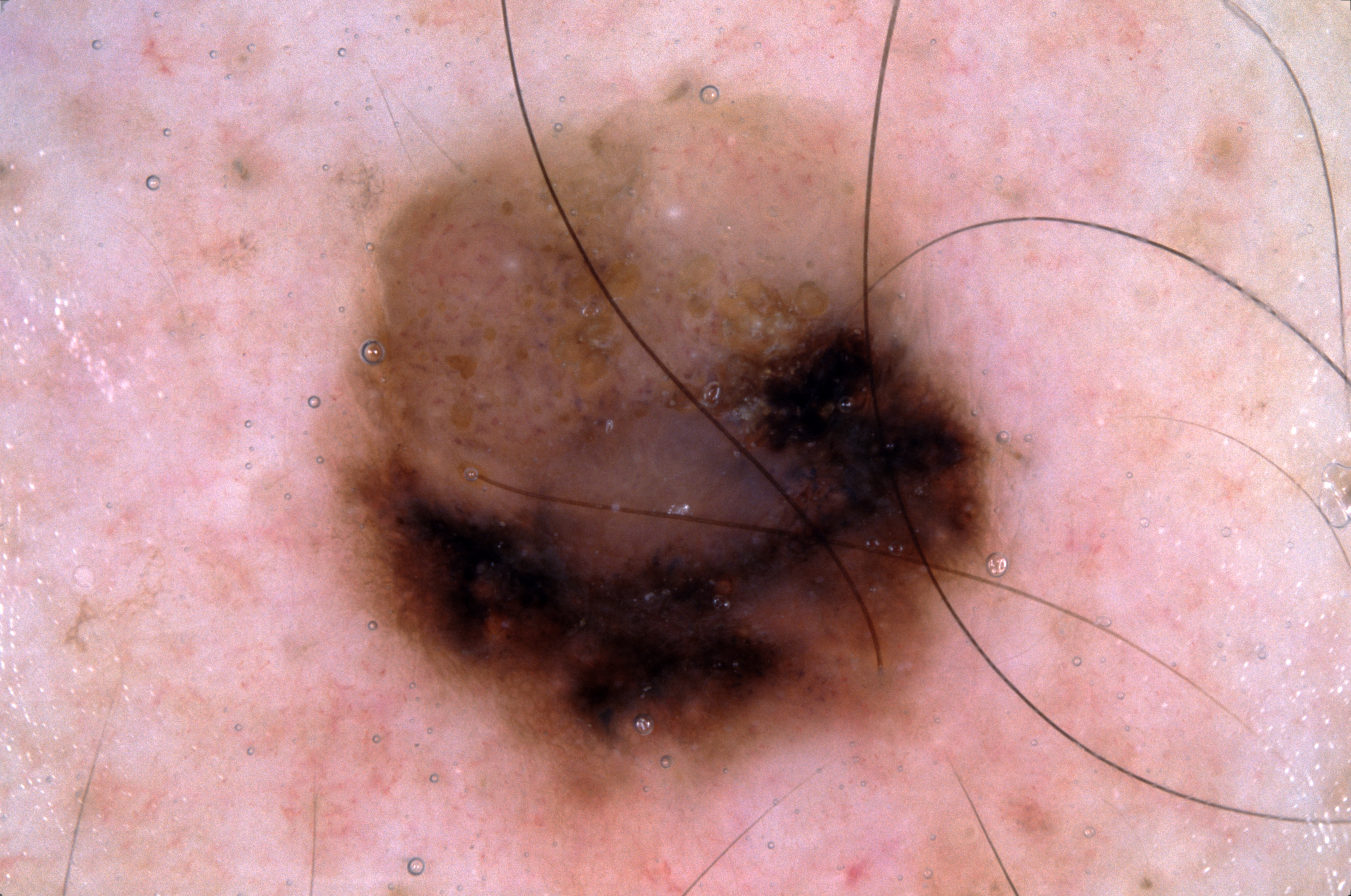Image and clinical context:
A dermoscopic close-up of a skin lesion. On dermoscopy, the lesion shows pigment network and milia-like cysts. Lesion location: bbox=[327, 91, 1003, 833].
Diagnosis:
Histopathological examination showed a melanoma, a skin cancer.